Skin tone: FST III; lay graders estimated MST 3. The patient indicates the lesion is rough or flaky and raised or bumpy. The affected area is the arm, back of the hand, front of the torso, leg and back of the torso. Close-up view. The condition has been present for less than one week — 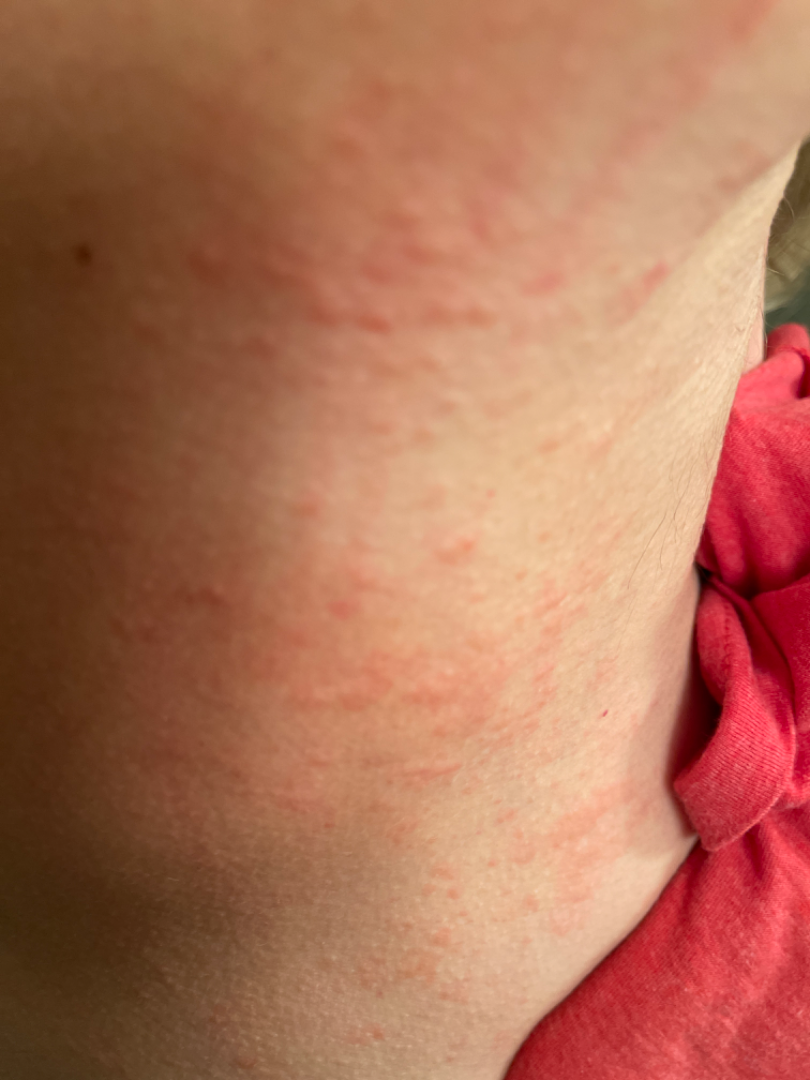<summary>
  <differential>
    <Allergic Contact Dermatitis>0.55</Allergic Contact Dermatitis>
    <Eczema>0.27</Eczema>
    <Folliculitis>0.18</Folliculitis>
  </differential>
</summary>